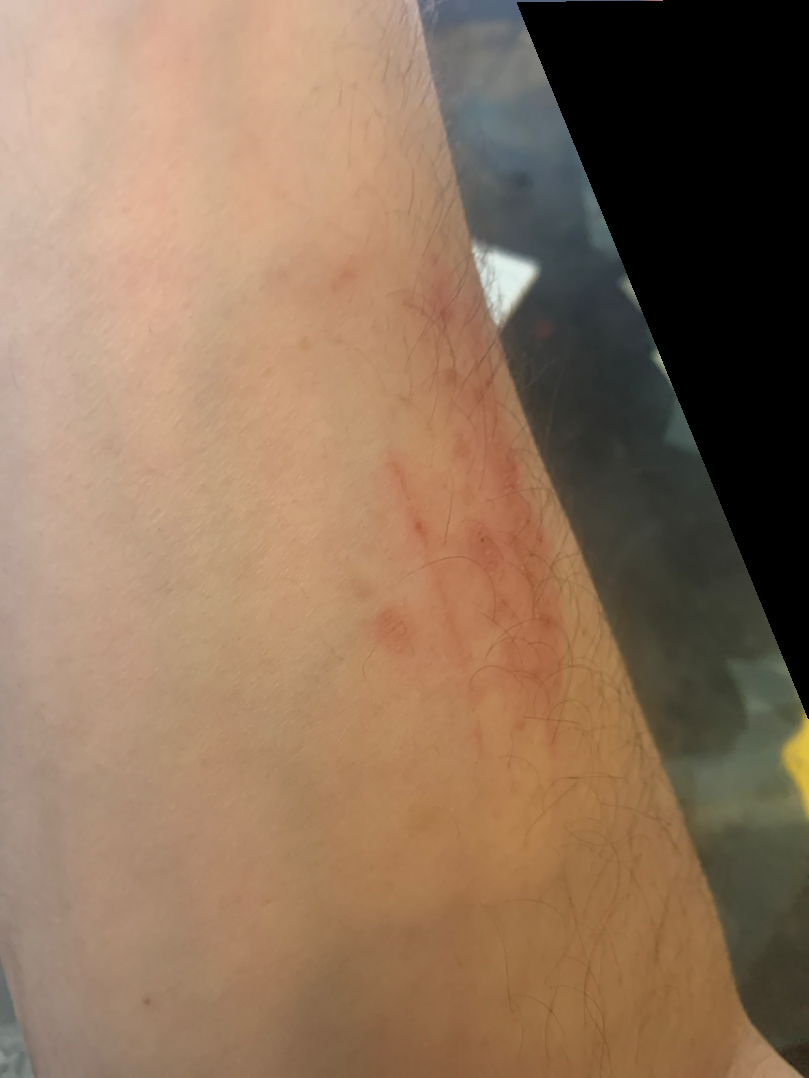No associated systemic symptoms reported. The contributor notes the lesion is raised or bumpy. Self-categorized by the patient as a rash. The photo was captured at an angle. Symptoms reported: bothersome appearance and itching. The affected area is the arm. The subject is male. Present for one to four weeks. On remote dermatologist review: the leading impression is Superficial wound of body region; also raised was Skin and soft tissue atypical mycobacterial infection; an alternative is SCC/SCCIS.